The lesion is described as flat · the photograph is a close-up of the affected area · skin tone: Fitzpatrick skin type IV · the affected area is the leg — 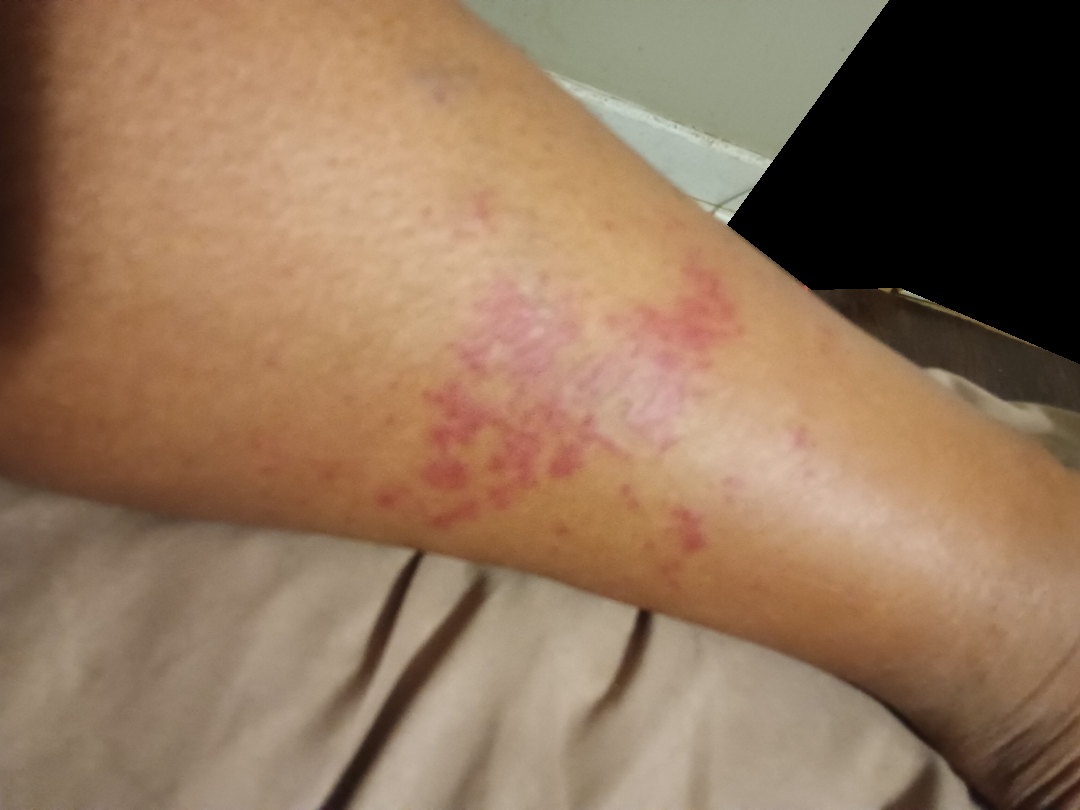Diagnostic features were not clearly distinguishable in this photograph.